A dermatoscopic image of a skin lesion: 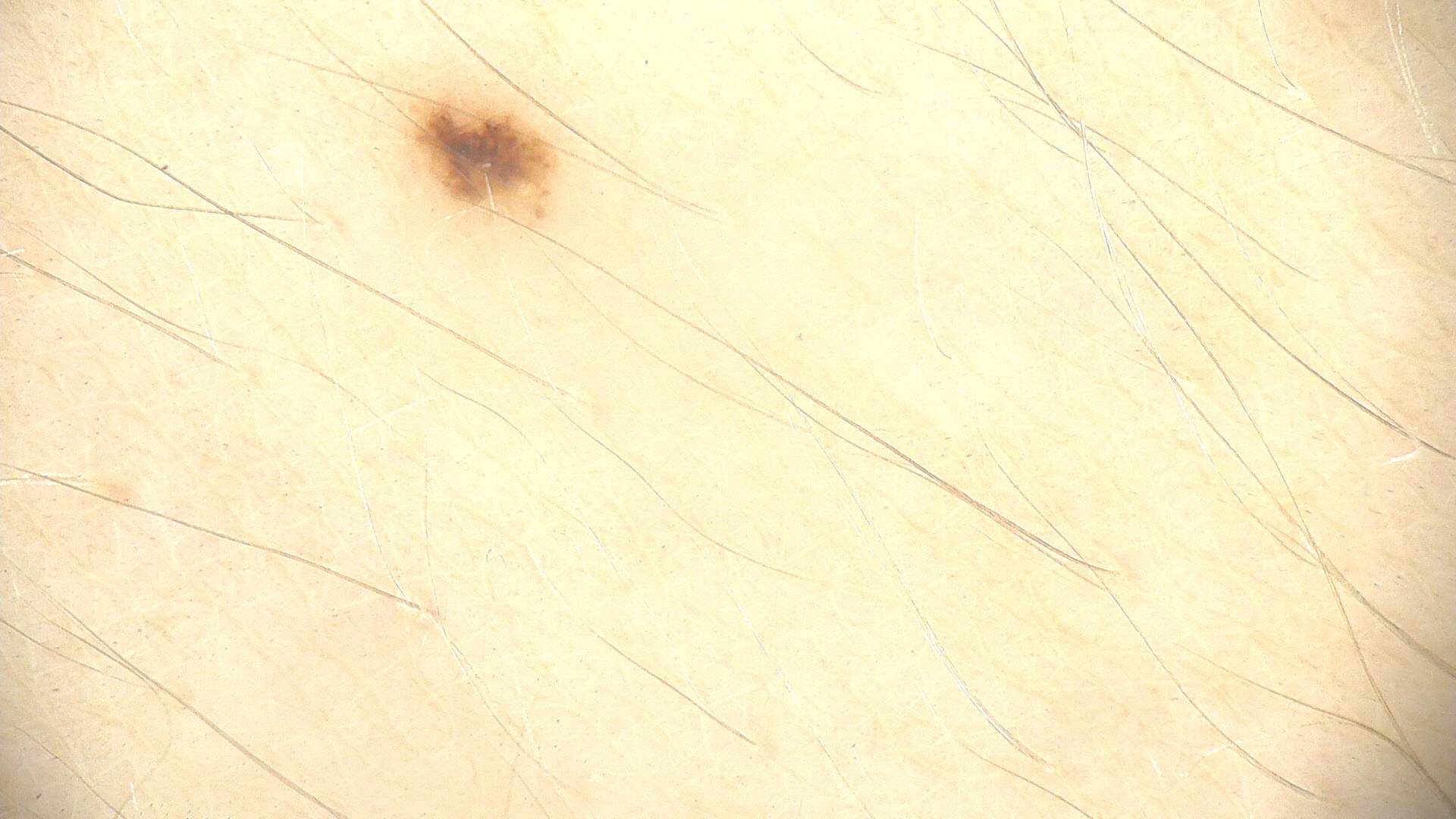Q: What was the diagnostic impression?
A: dysplastic junctional nevus (expert consensus)